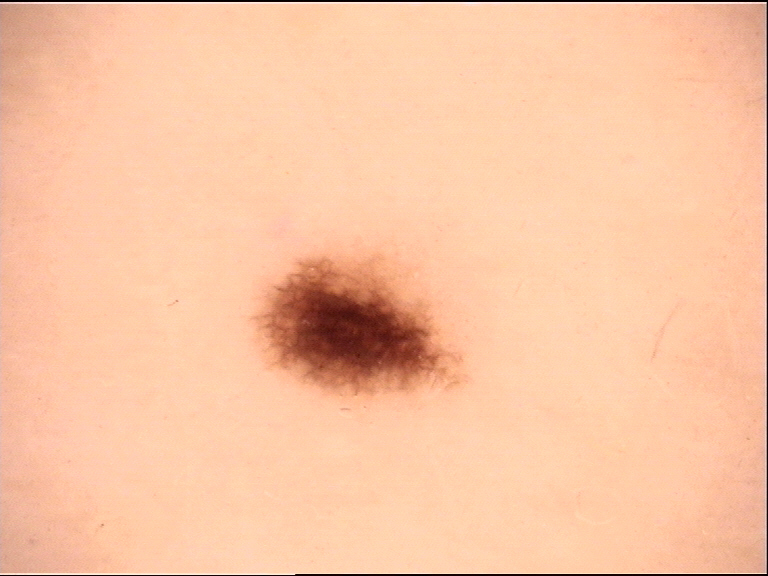Case:
A dermoscopic image of a skin lesion.
Impression:
Diagnosed as a benign lesion — a dysplastic junctional nevus.